Self-categorized by the patient as a rash · this image was taken at an angle · the affected area is the arm · symptoms reported: itching and enlargement: 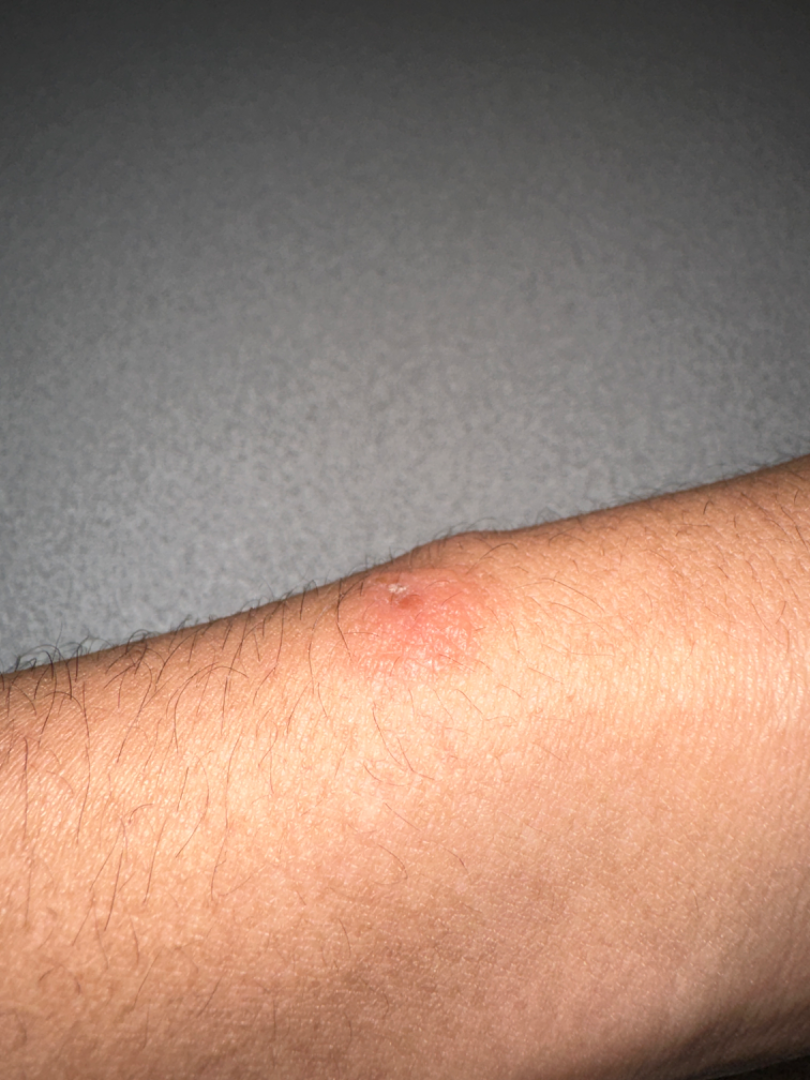On photographic review by a dermatologist: Allergic Contact Dermatitis (primary).